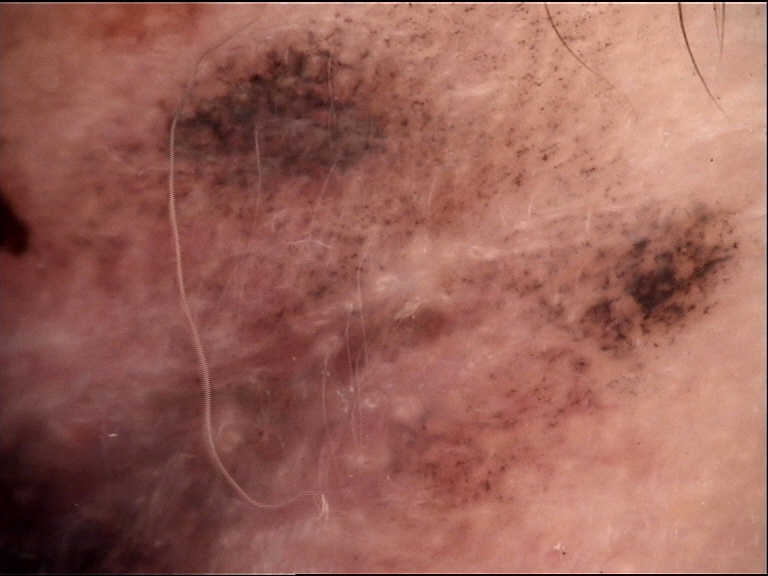A dermoscopy image of a single skin lesion. Confirmed on histopathology as a malignant lesion — a lentigo maligna.